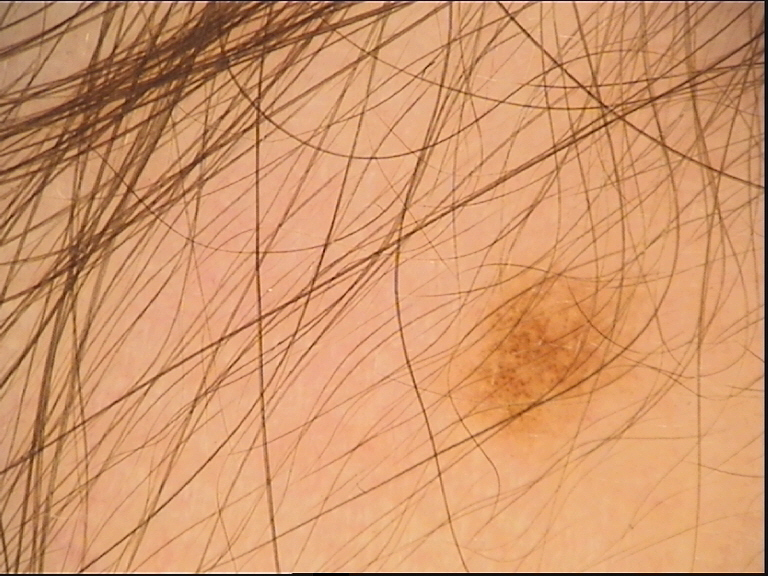A skin lesion imaged with a dermatoscope.
The diagnostic label was a benign lesion — a dysplastic junctional nevus.